This is a close-up image — 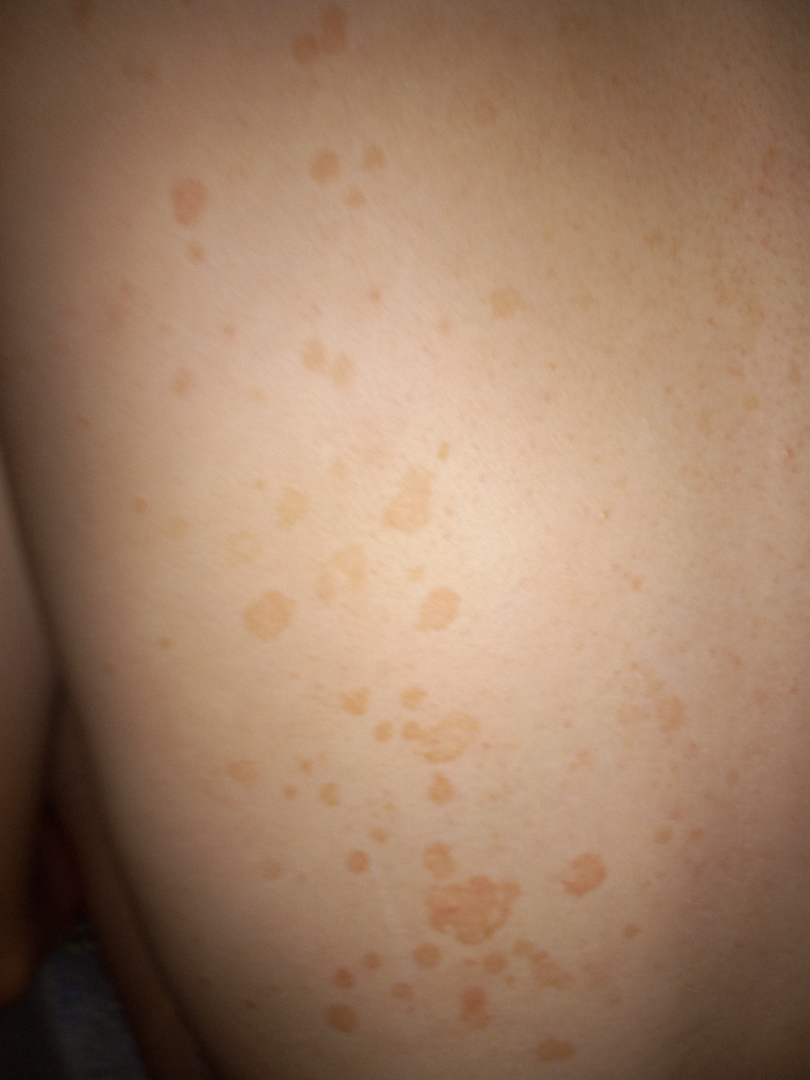Case summary:
– skin tone — Fitzpatrick III
– differential diagnosis — Tinea Versicolor (favored); SK/ISK (possible); Lentigo (remote)